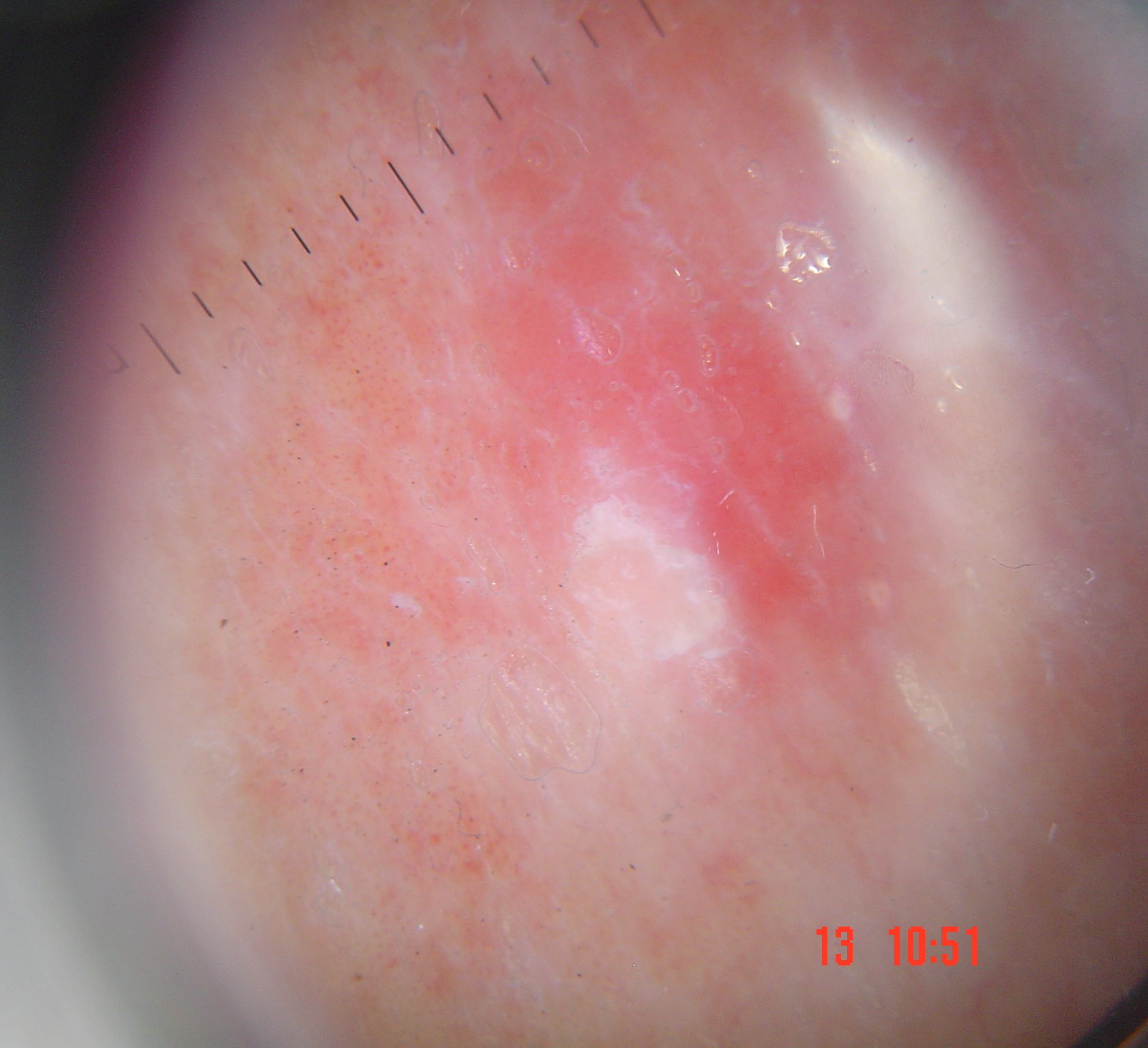category: keratinocytic; diagnosis: Bowen's disease (biopsy-proven).